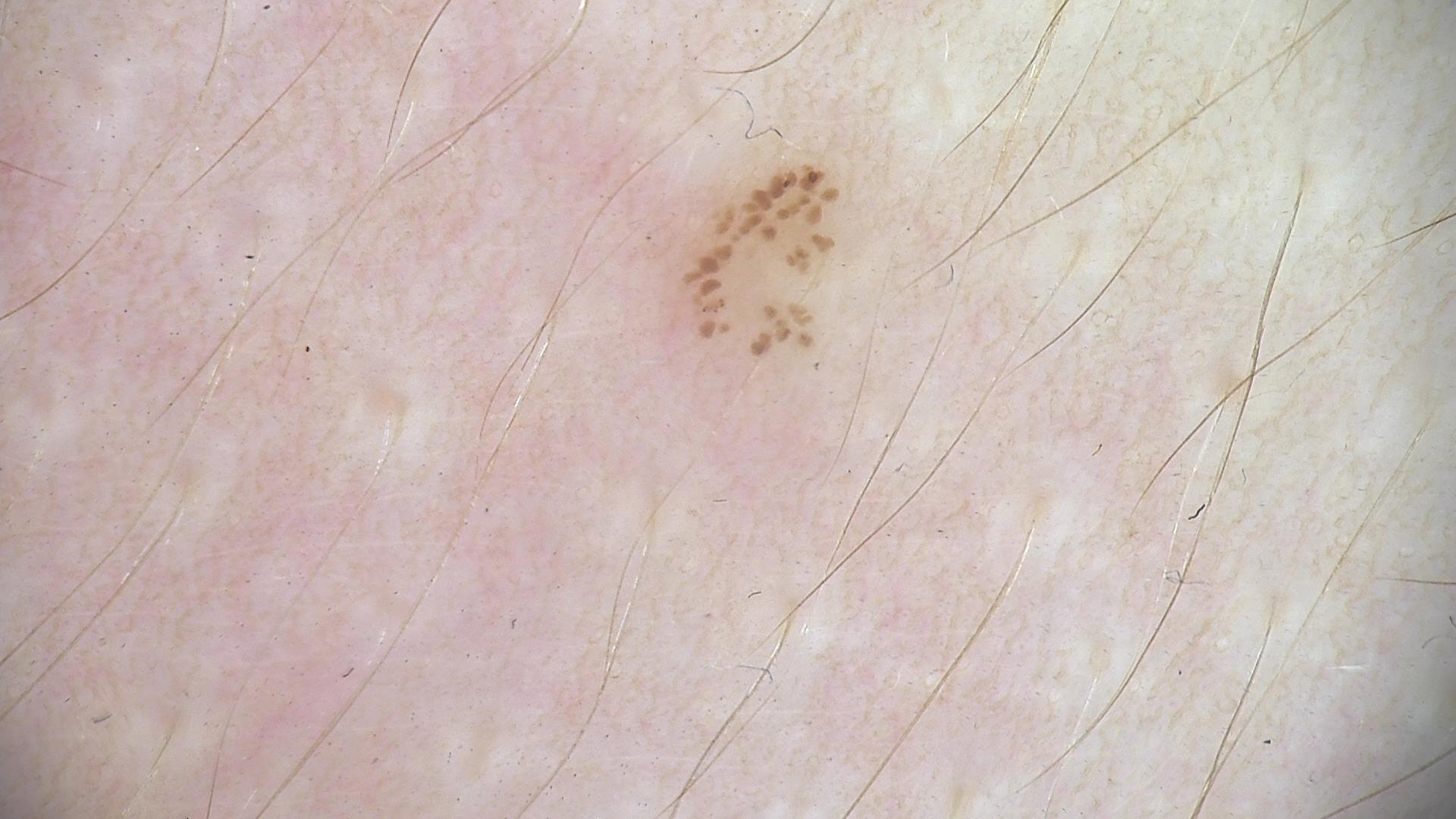A dermoscopic photograph of a skin lesion.
The diagnostic label was a dysplastic junctional nevus.